Female patient, age 40–49; located on the head or neck; the photograph is a close-up of the affected area: 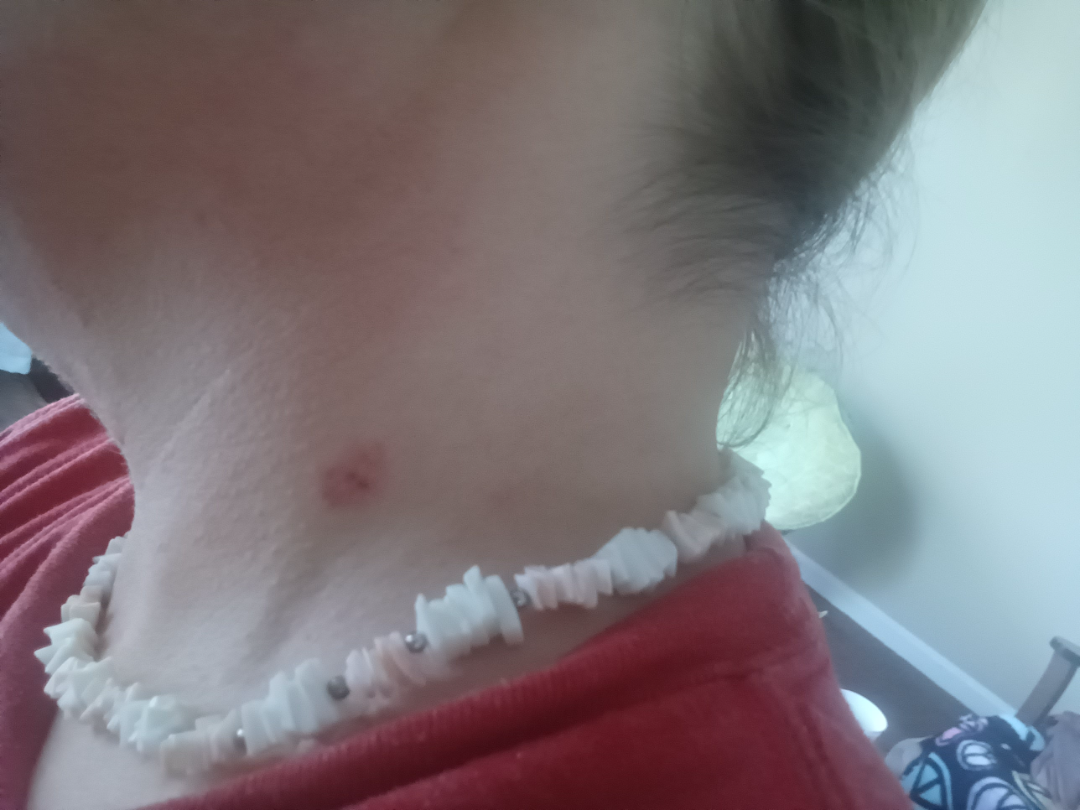assessment — not assessable; present for — less than one week; patient-reported symptoms — bothersome appearance; described texture — raised or bumpy.